Collected as part of a research study, without a referral diagnosis · the patient describes having a moderate number of moles · the patient says their skin reddens with sun exposure · a skin lesion imaged with a dermatoscope · a female subject 59 years old: 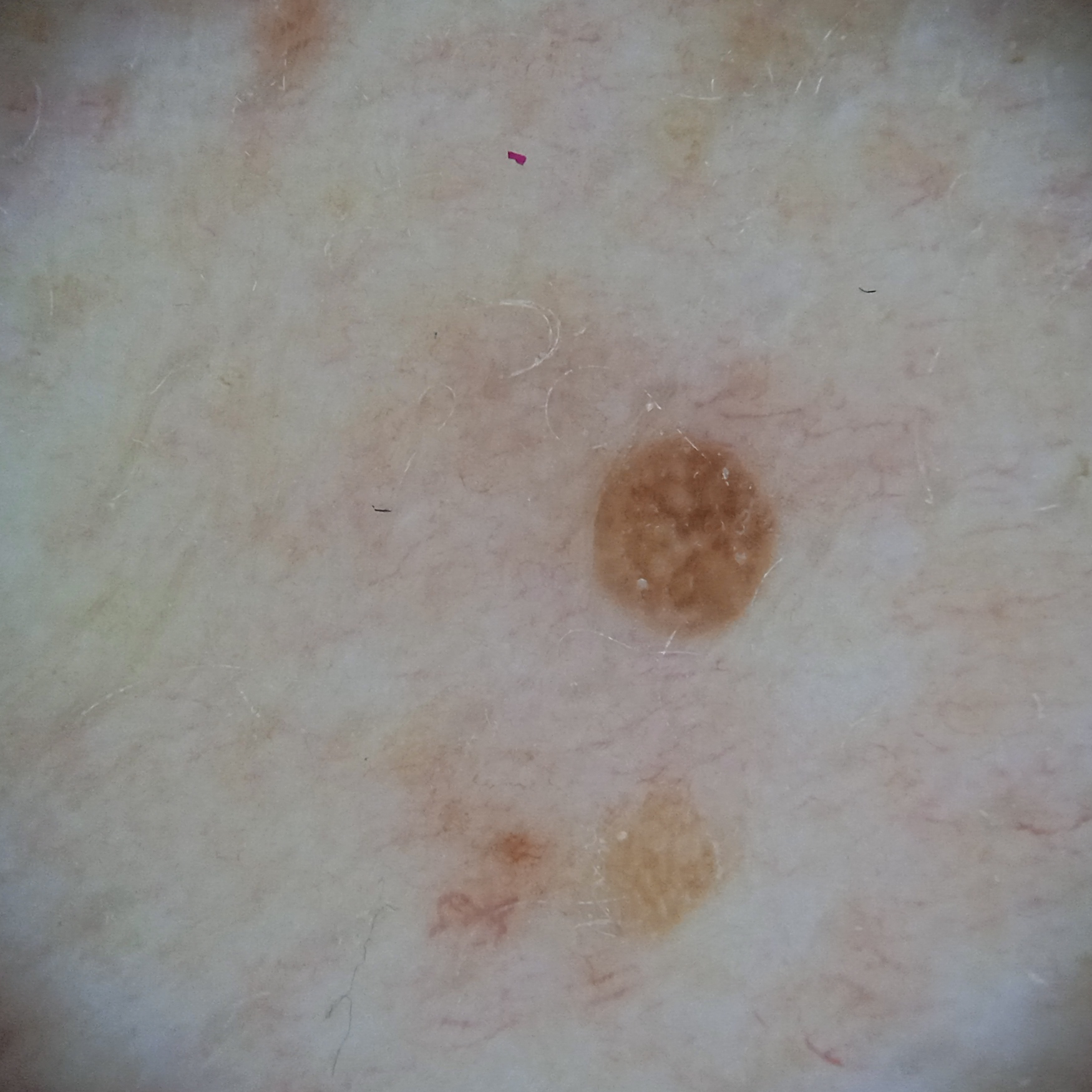body site: the torso
assessment: seborrheic keratosis (dermatologist consensus)